A dermoscopic image of a skin lesion: 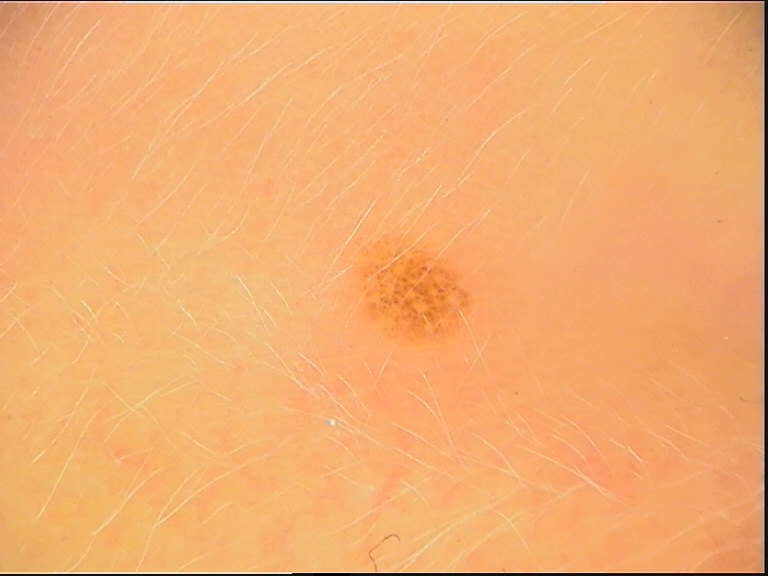Classified as a benign lesion — a dysplastic junctional nevus.